This is a close-up image: 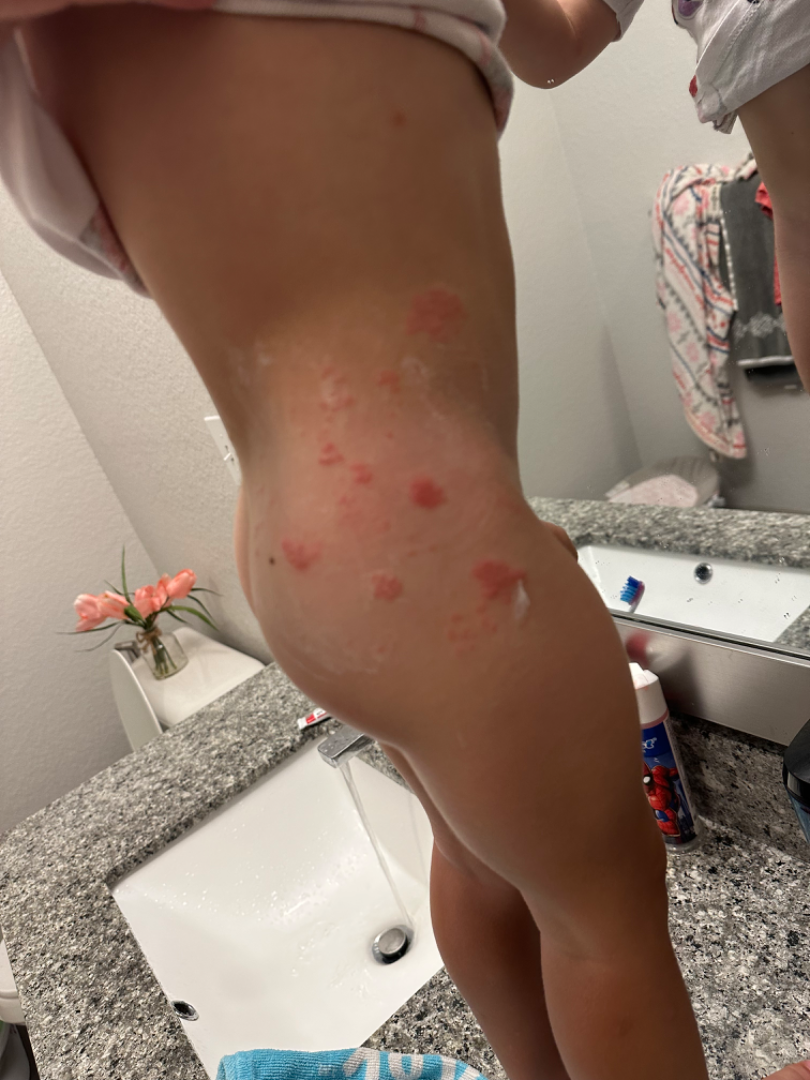On photographic review by a dermatologist, Acute dermatitis, NOS (primary).